The photo was captured at an angle; the lesion involves the front of the torso and back of the torso — 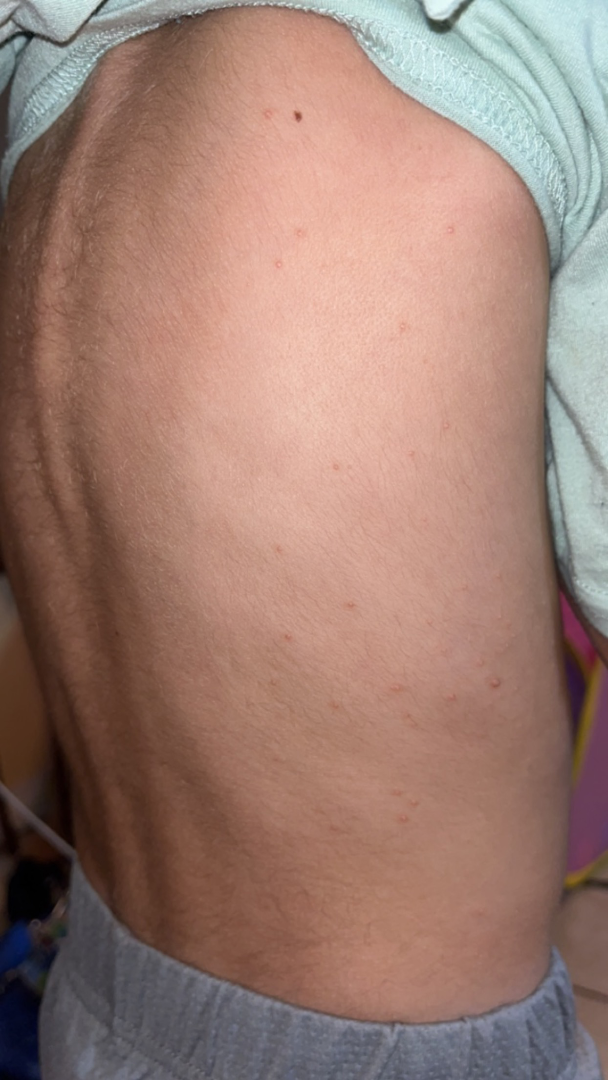Diagnostic features were not clearly distinguishable in this photograph.
The condition has been present for about one day.
The lesion is described as fluid-filled and raised or bumpy.